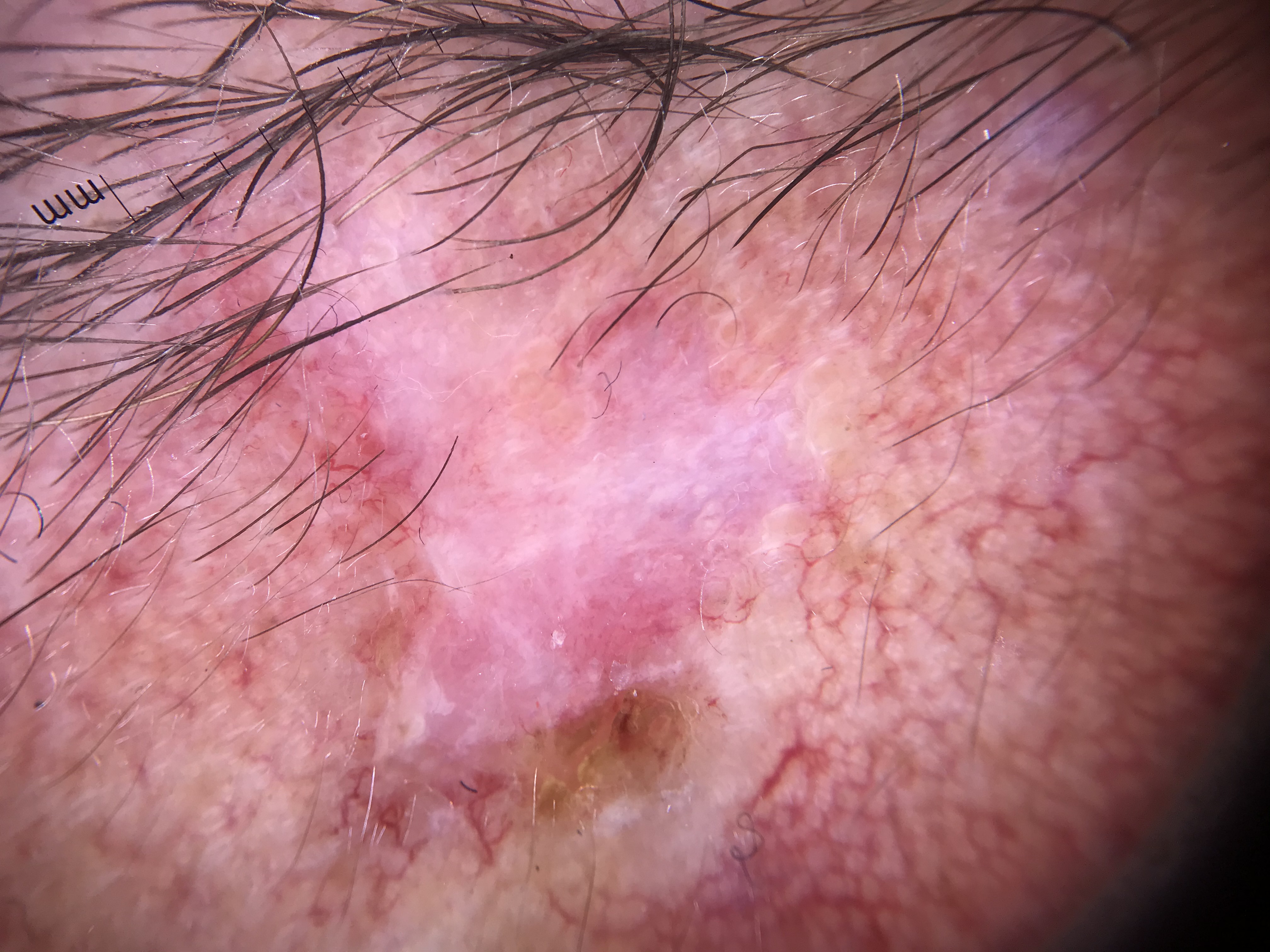A dermoscopic image of a skin lesion. Biopsy-confirmed as a malignant, keratinocytic lesion — a basal cell carcinoma.